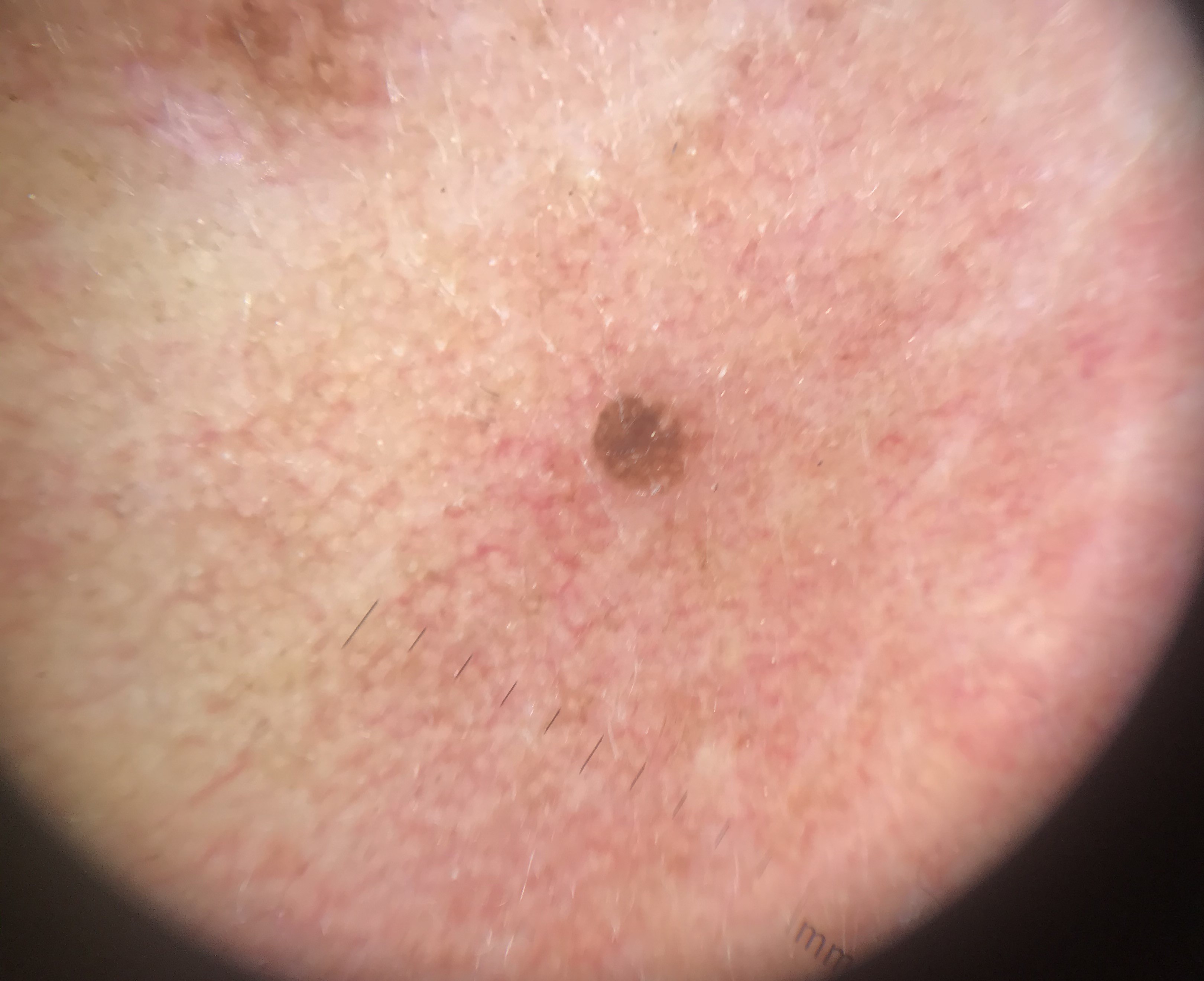A dermatoscopic image of a skin lesion.
Consistent with a seborrheic keratosis.